A clinical photograph showing a skin lesion; imaged for a research study, with no referral diagnosis recorded; a female subject age 67.
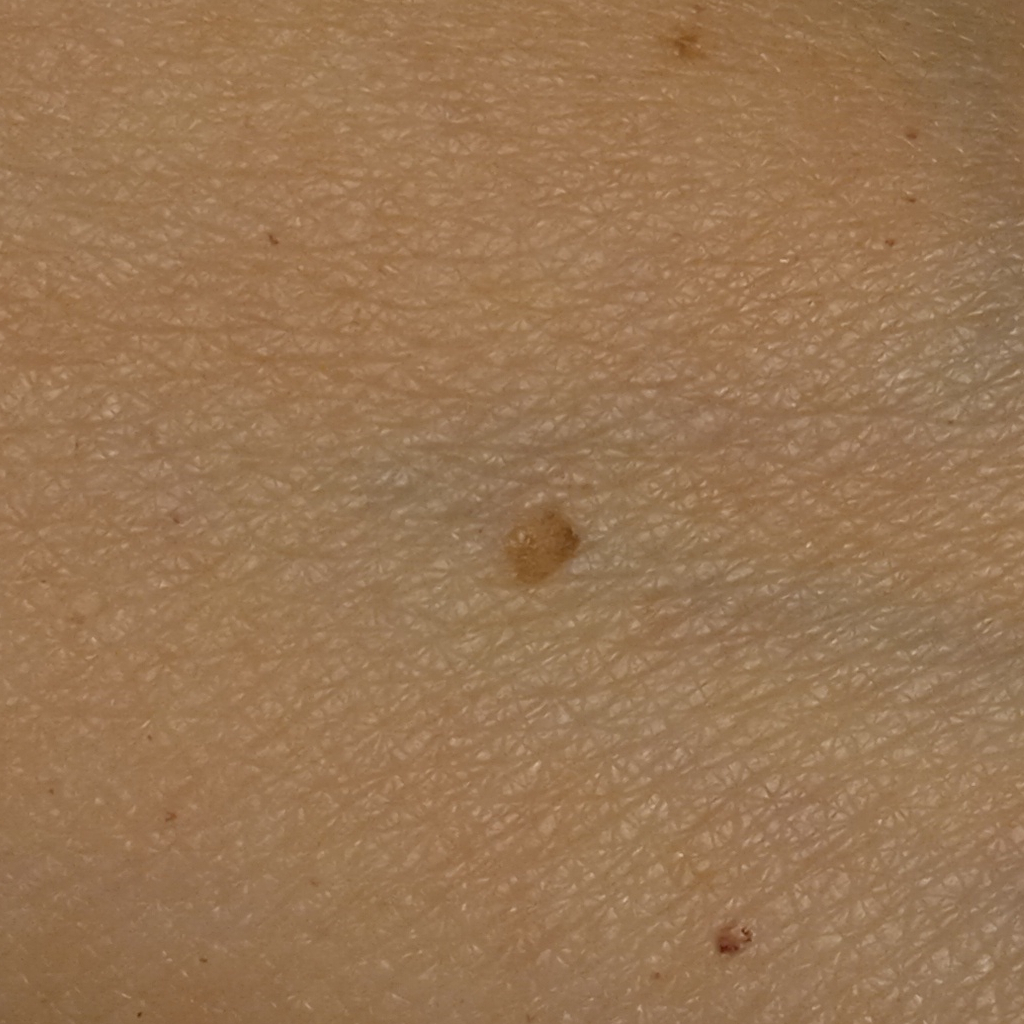* body site · an arm
* size · 3.1 mm
* diagnostic label · seborrheic keratosis (dermatologist consensus)